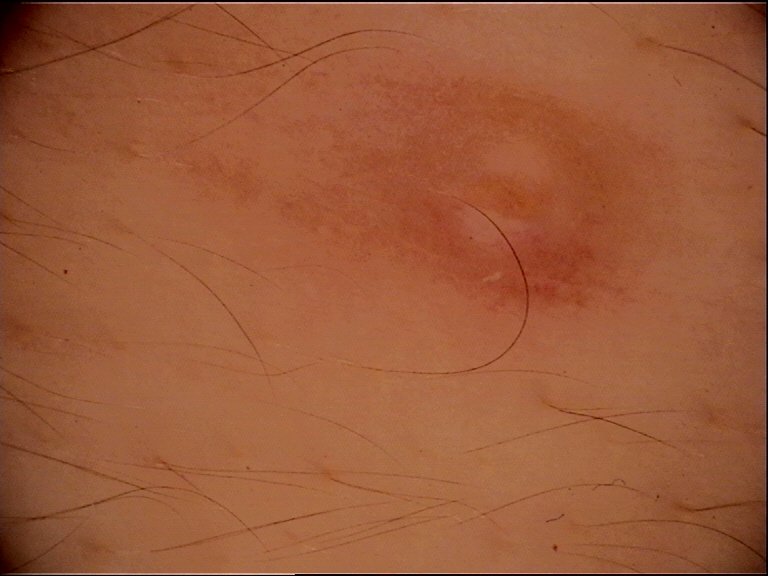Q: What was the diagnostic impression?
A: dermal nevus (expert consensus)